The affected area is the arm; this image was taken at an angle — 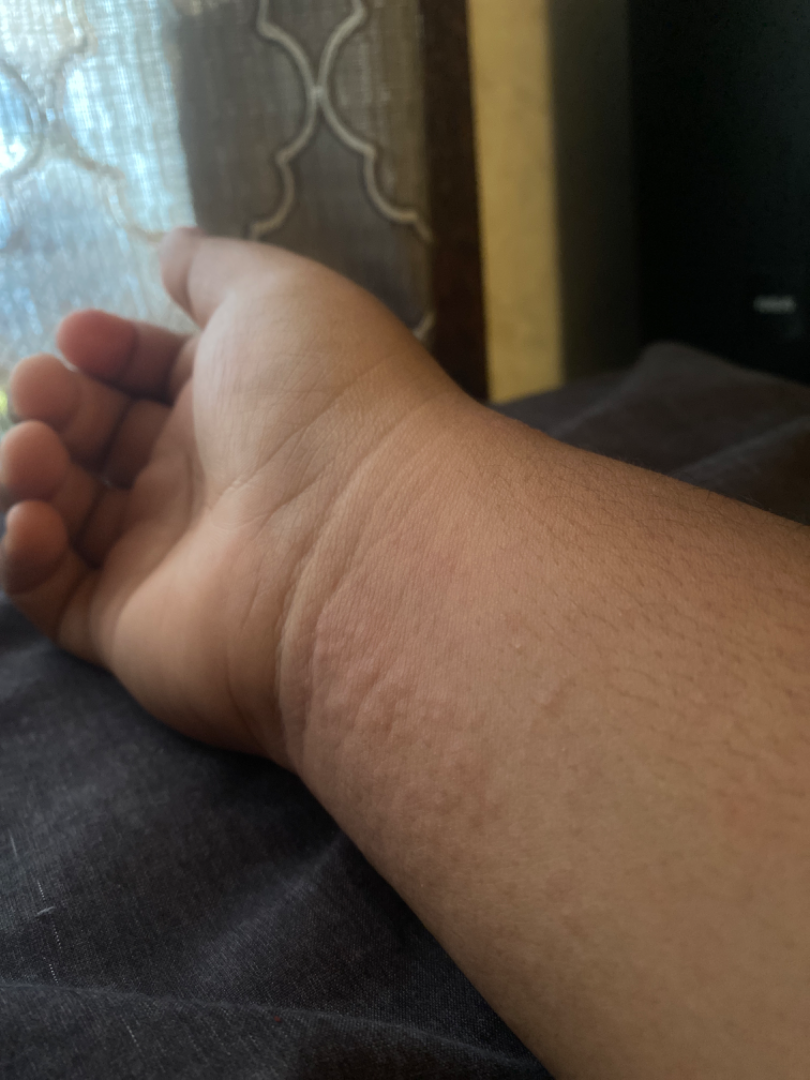{
  "assessment": "ungradable on photographic review"
}